A skin lesion imaged with a dermatoscope. The patient is a male aged around 70 — 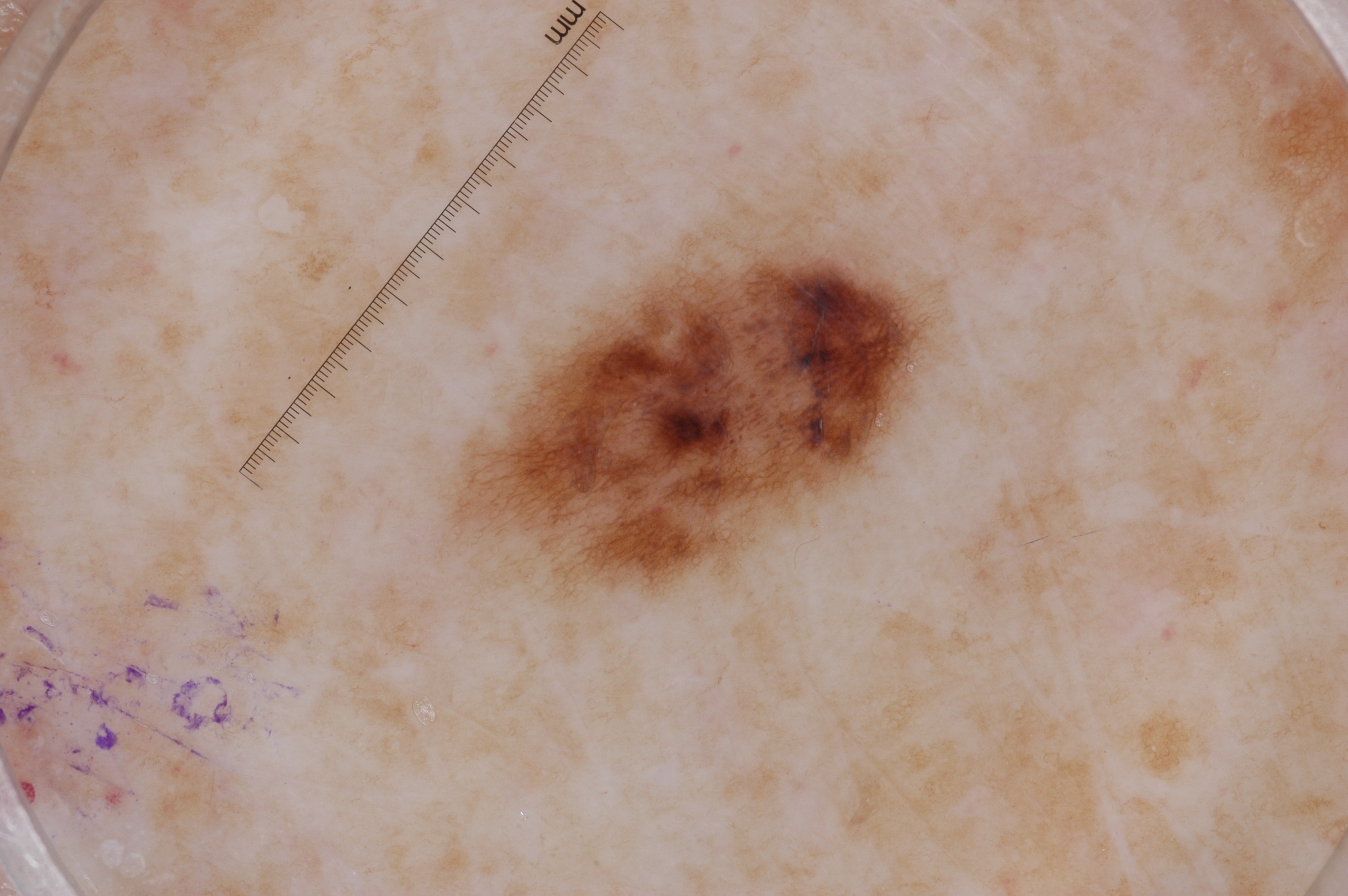Findings:
Dermoscopy demonstrates pigment network. With coordinates (x1, y1, x2, y2), the lesion is located at bbox(439, 186, 952, 606).
Impression:
The lesion was assessed as a melanocytic nevus, a benign lesion.